A female patient aged 59. A clinical photograph of a skin lesion: 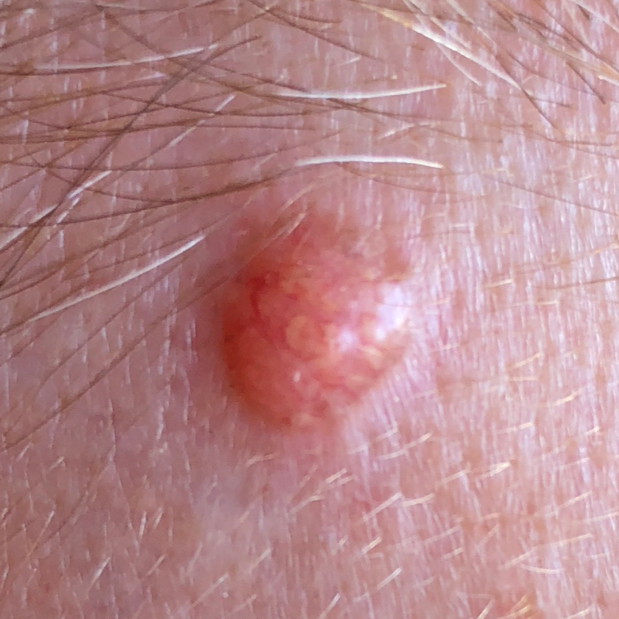Q: Where on the body is the lesion?
A: the face
Q: What is the diagnosis?
A: basal cell carcinoma (biopsy-proven)